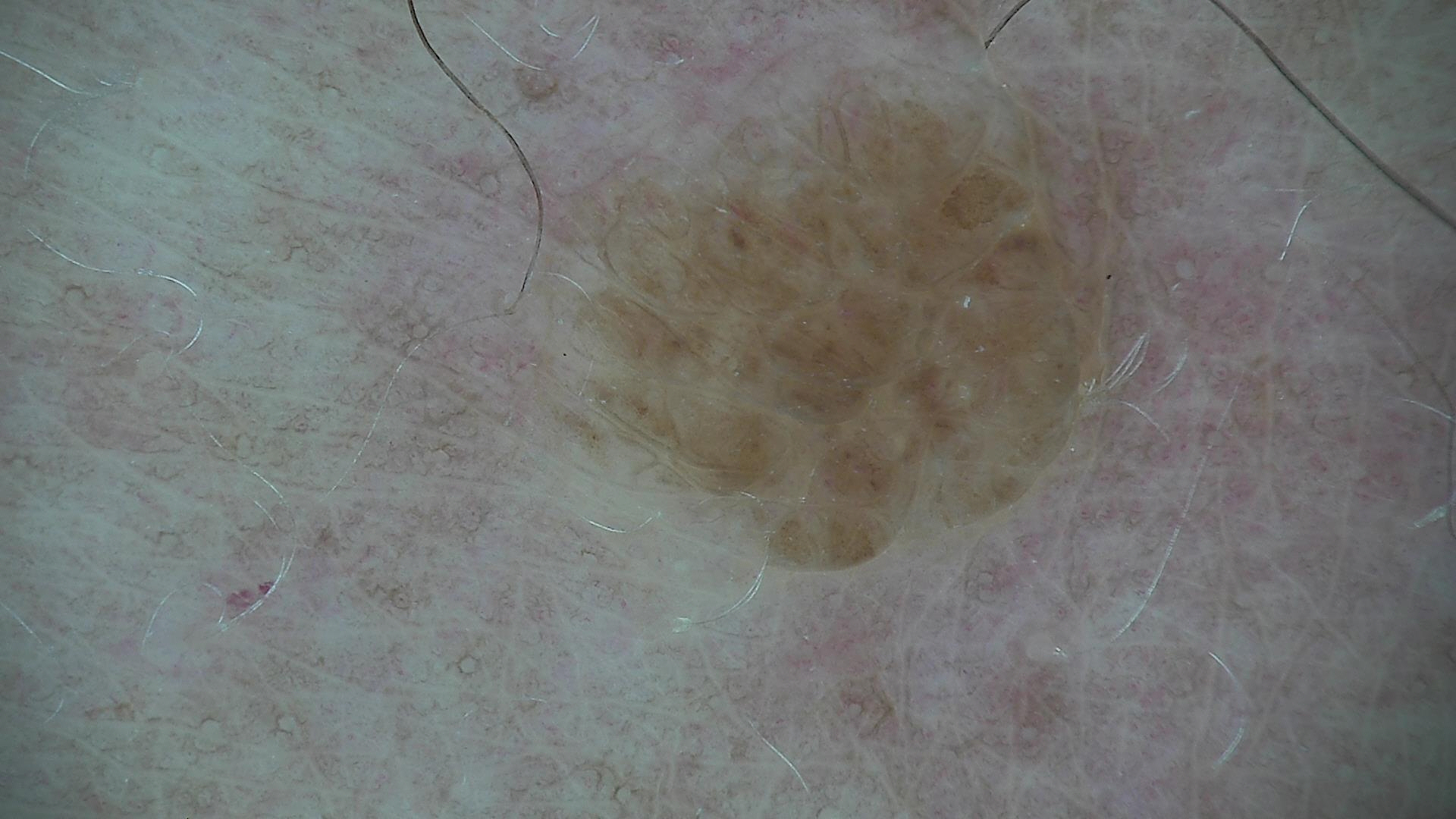The diagnostic label was a seborrheic keratosis.